A dermoscopic close-up of a skin lesion: 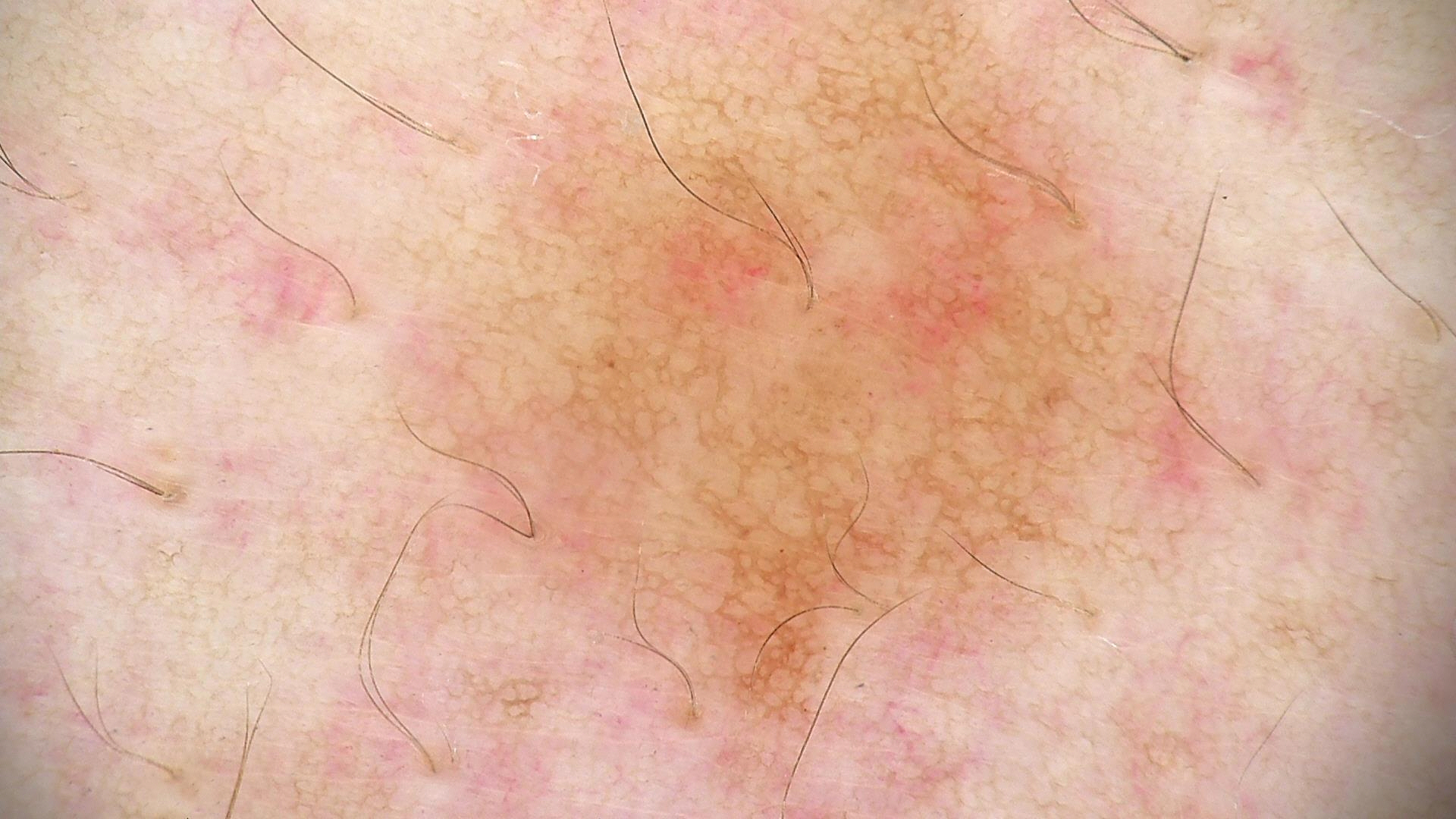diagnosis = dysplastic junctional nevus (expert consensus).